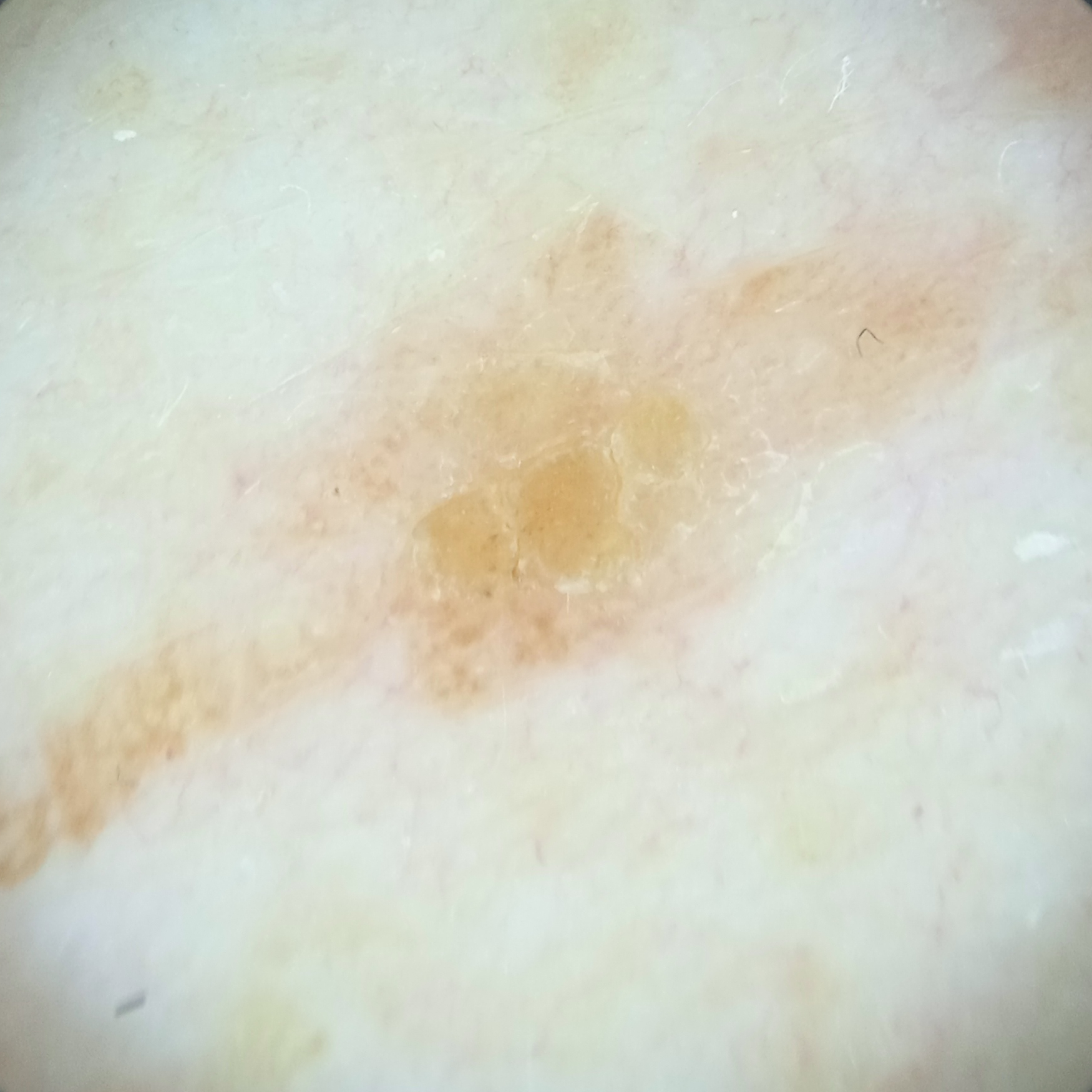{"patient": {"age": 83, "sex": "male"}, "image": "dermoscopic image", "referral": "research study (no referral diagnosis)", "risk_factors": {"negative": ["no personal history of skin cancer"]}, "sun_reaction": "skin reddens with sun exposure", "lesion_location": "the back", "lesion_size": {"diameter_mm": 16.4}, "diagnosis": {"name": "seborrheic keratosis", "malignancy": "benign"}}